Close-up view: 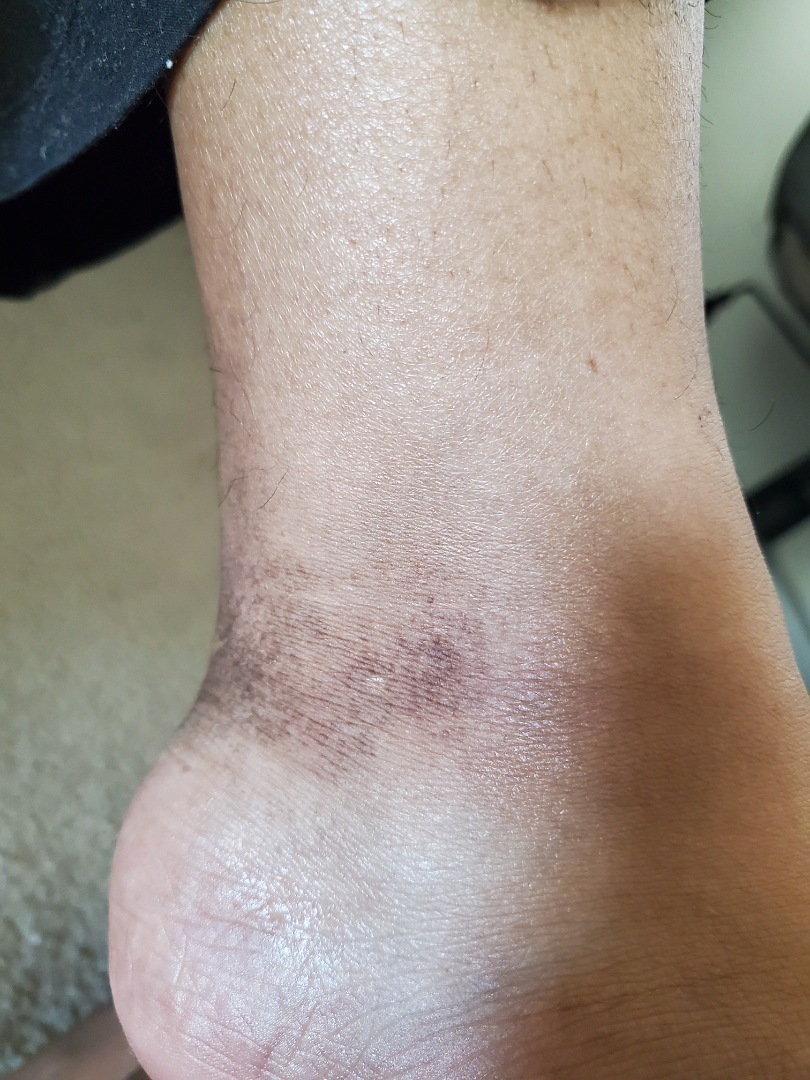{
  "assessment": "ungradable on photographic review",
  "skin_tone": {
    "fitzpatrick": "V",
    "monk_skin_tone": [
      3,
      4
    ]
  }
}